A dermoscopic photograph of a skin lesion: 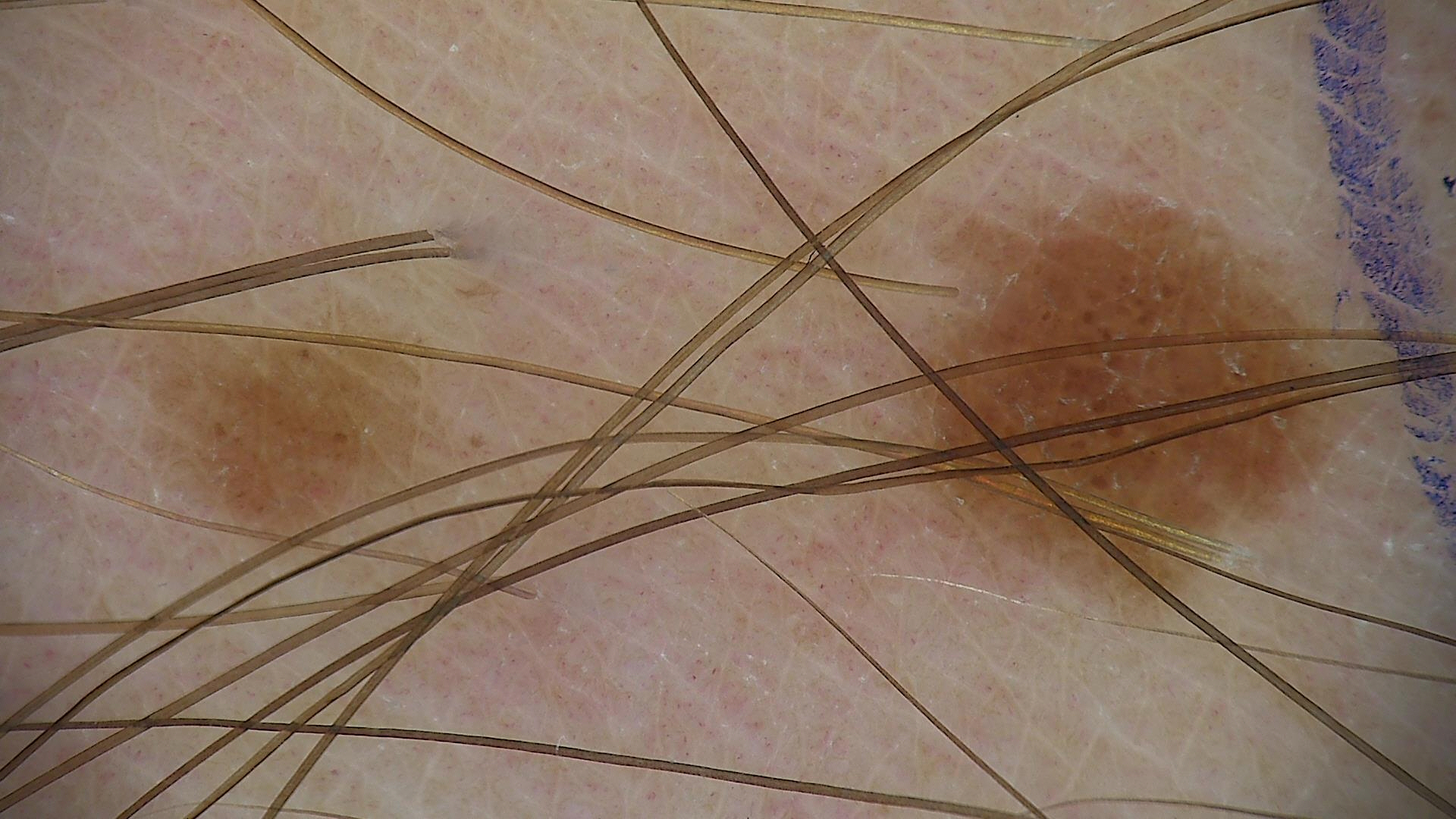Case:
- diagnostic label · junctional nevus (expert consensus)